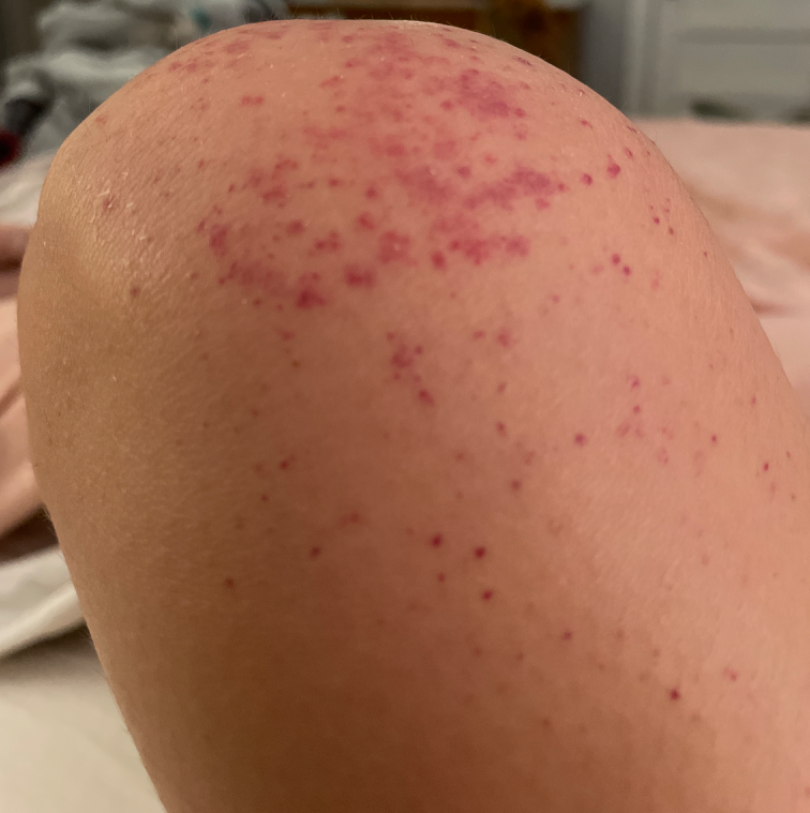Findings: No differential diagnosis could be assigned on photographic review. Background: Texture is reported as raised or bumpy and rough or flaky. The patient indicates burning and itching. The contributor is 30–39, female. An image taken at an angle. Self-categorized by the patient as a rash.